This is a close-up image. The patient is male. The patient notes itching and bothersome appearance. The patient described the issue as a rash. Located on the arm. Self-reported Fitzpatrick skin type II; non-clinician graders estimated Monk skin tone scale 4 — 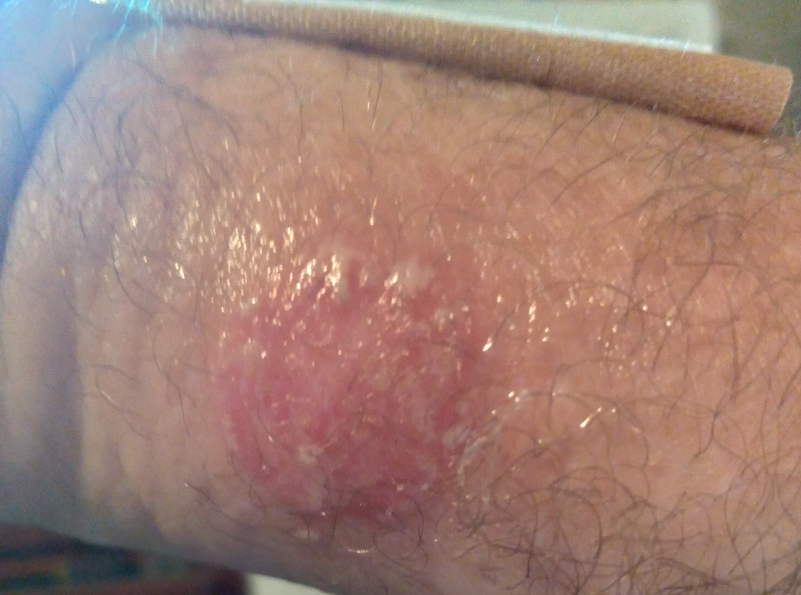Review: The image was not sufficient for the reviewer to characterize the skin condition.